A clinical photograph showing a skin lesion:
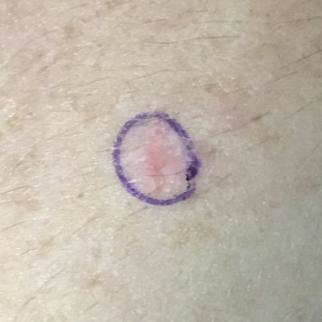site: a forearm, impression: actinic keratosis (clinical consensus).